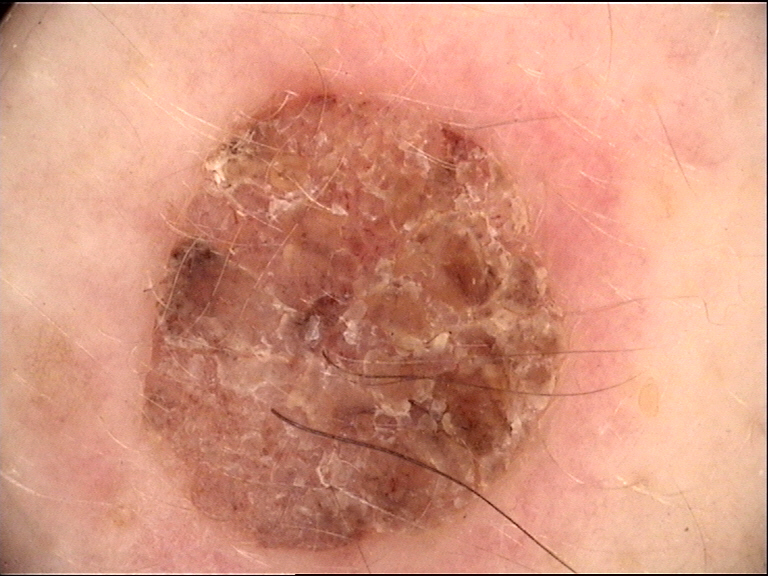diagnostic label = dermal nevus (expert consensus).